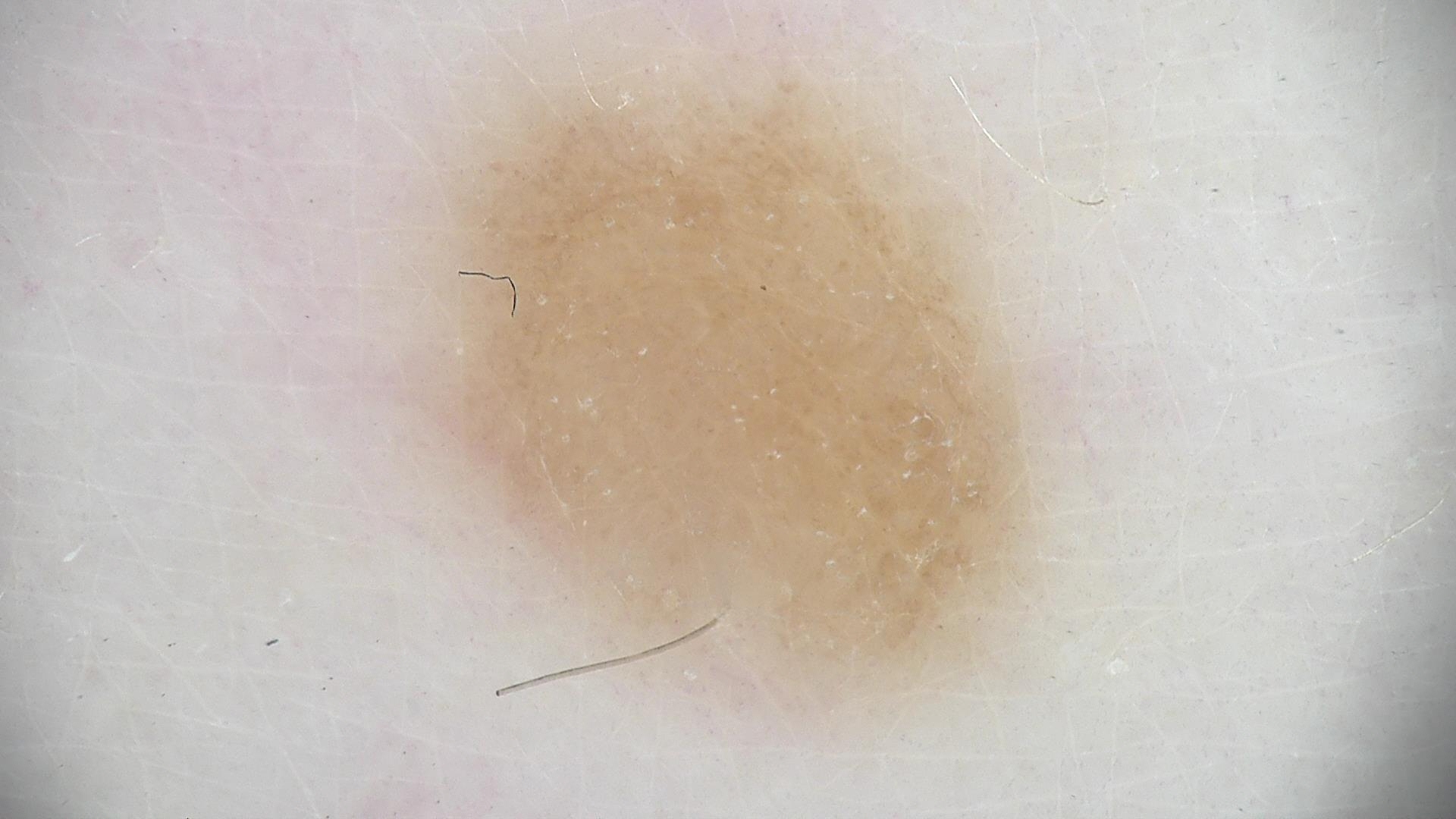The architecture is that of a banal lesion. Diagnosed as a dermal nevus.